Self-categorized by the patient as a rash, no constitutional symptoms were reported, symptoms reported: itching, located on the arm, texture is reported as raised or bumpy, close-up view — 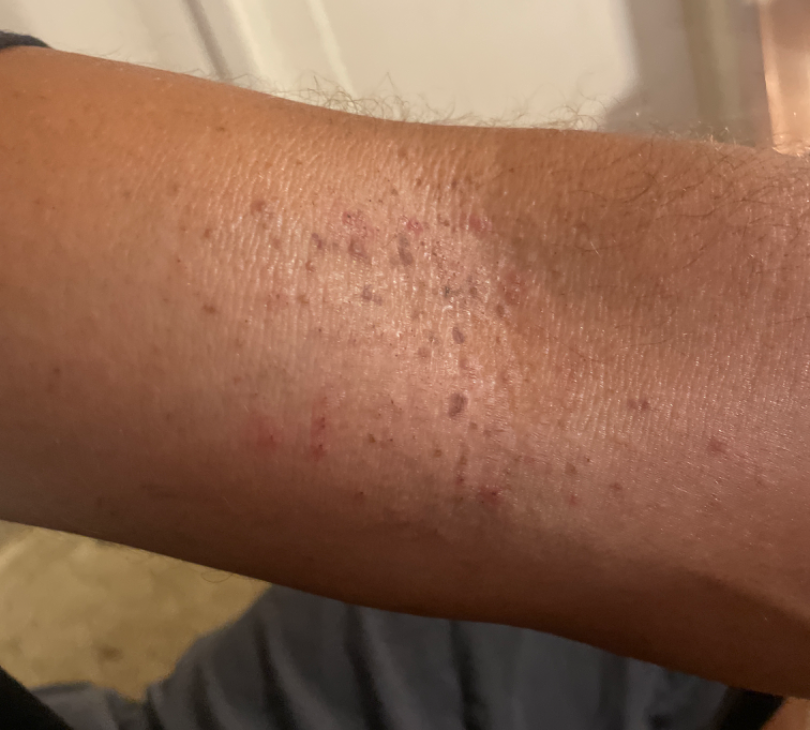assessment: ungradable on photographic review.